A dermoscopic image of a skin lesion.
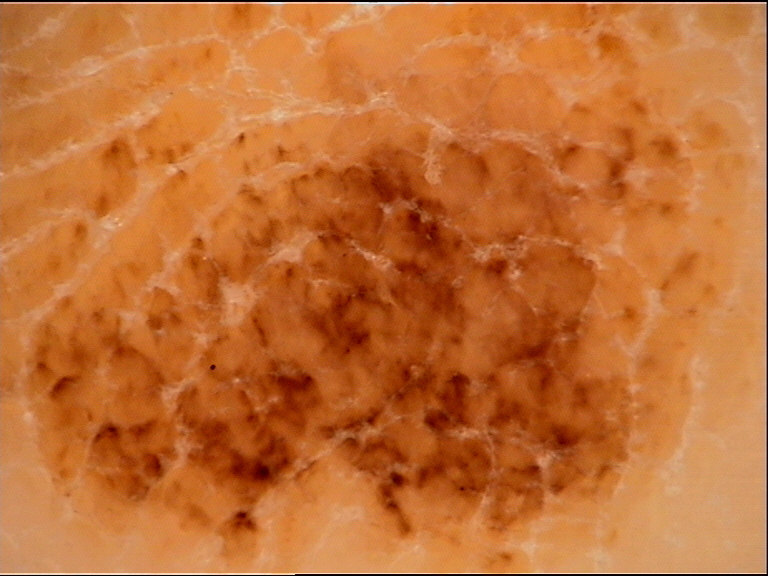Consistent with an acral dysplastic compound nevus.